A close-up photograph, the lesion involves the arm, no constitutional symptoms were reported, skin tone: Fitzpatrick III; lay graders estimated Monk skin tone scale 4 (US pool) or 3 (India pool), the lesion is associated with itching, the patient reports the lesion is raised or bumpy, reported duration is less than one week:
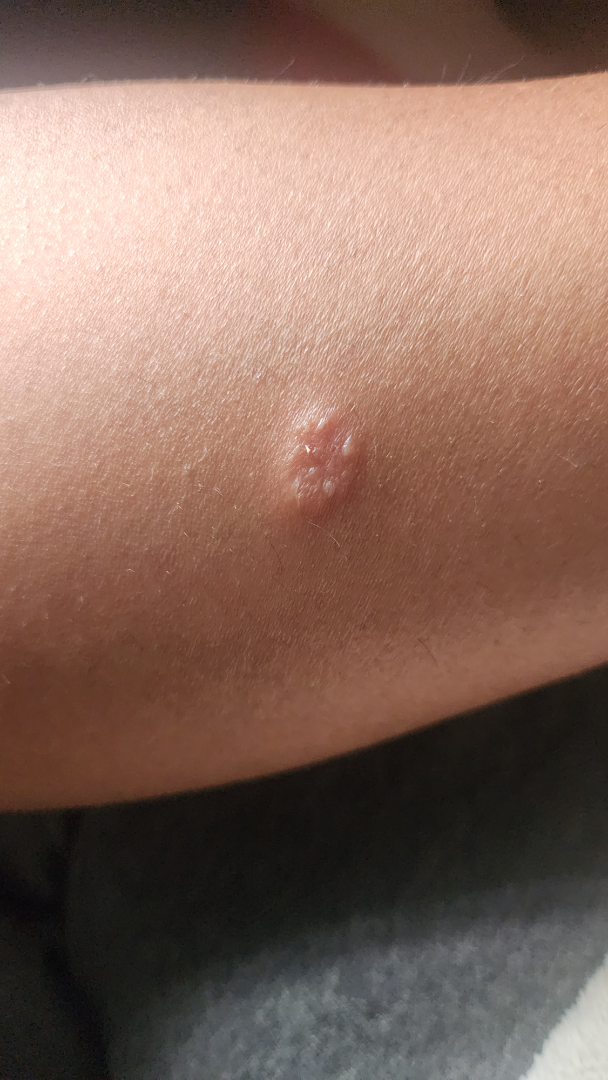Impression: The dermatologist could not determine a likely condition from the photograph alone.